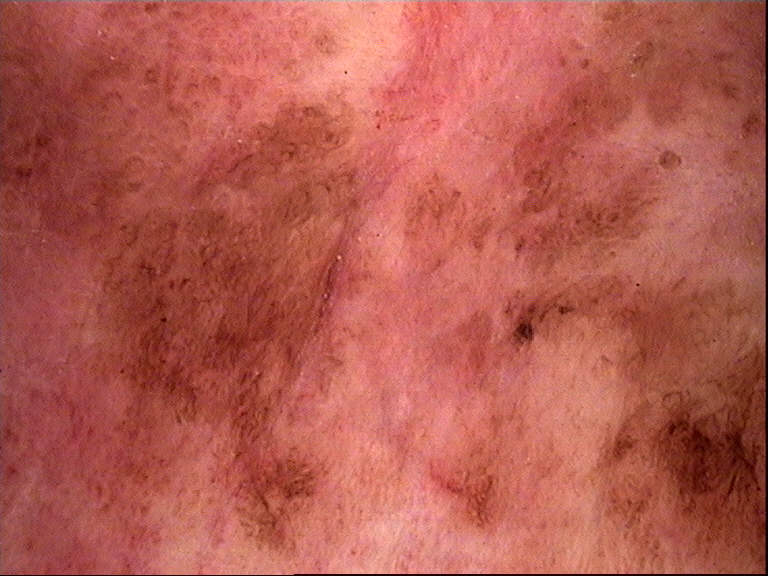This is a keratinocytic lesion. Confirmed on histopathology as Bowen's disease.